A clinical close-up photograph of a skin lesion:
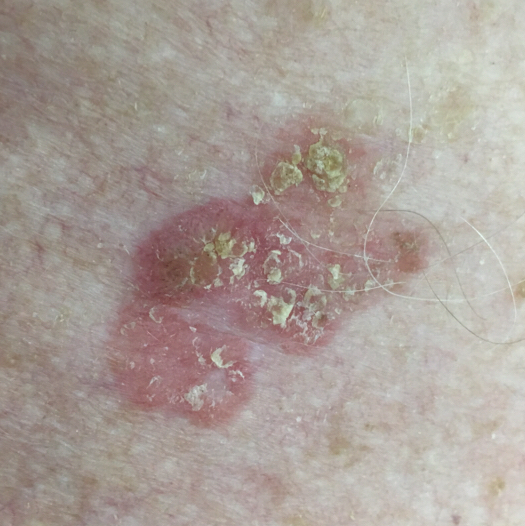The lesion involves an ear. The lesion measures 20 × 18 mm. Biopsy-confirmed as a squamous cell carcinoma.